This image was taken at a distance:
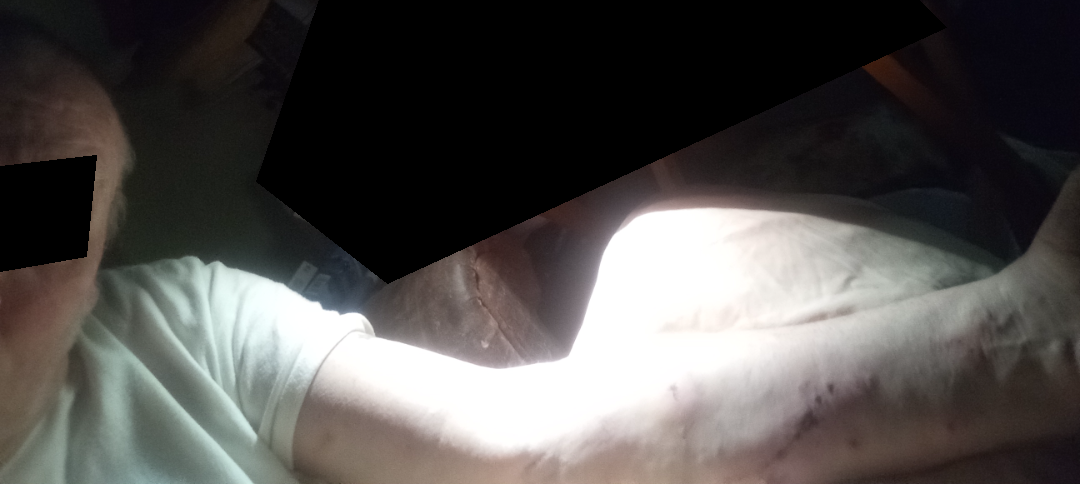assessment — ungradable on photographic review